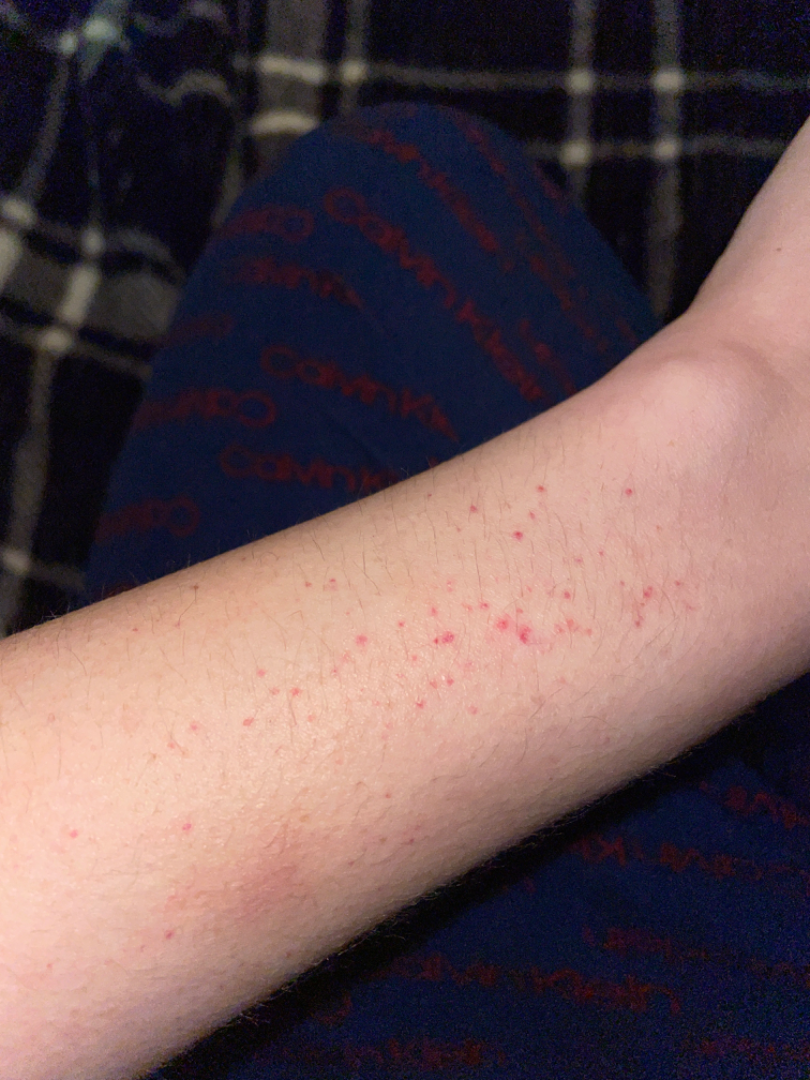Most likely petechiae; an alternative is Pigmented purpuric eruption; the differential also includes Leukocytoclastic Vasculitis.